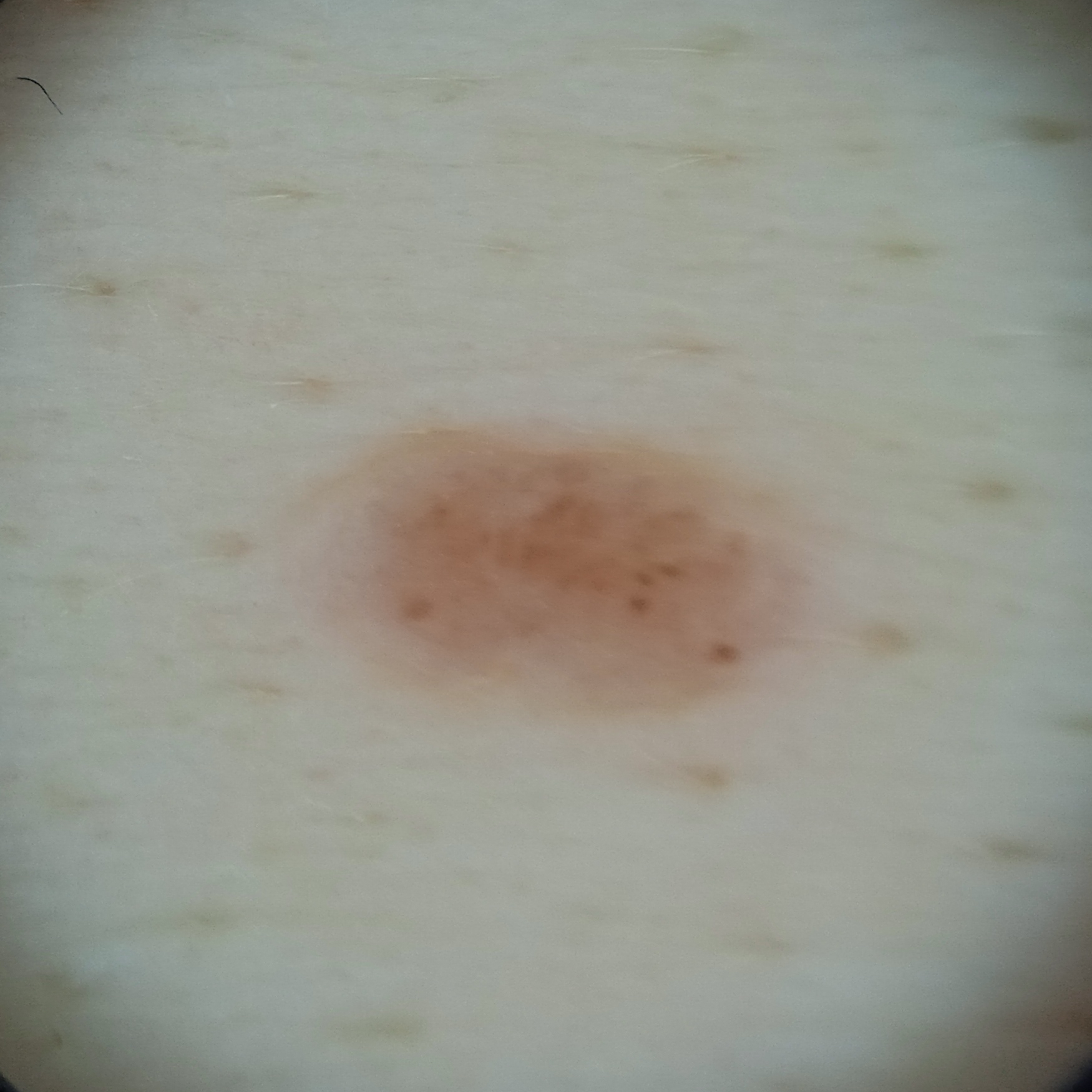Dermatologist review favored a melanocytic nevus.